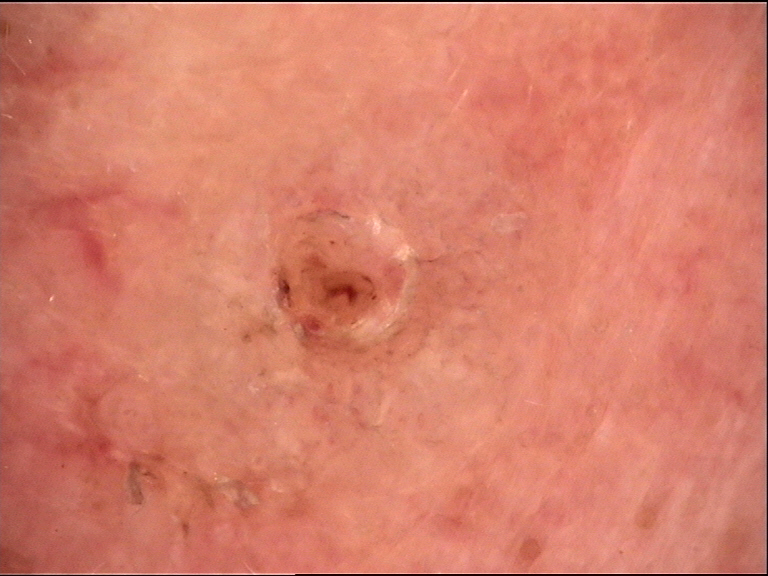Histopathology confirmed a basal cell carcinoma.